An image taken at a distance — 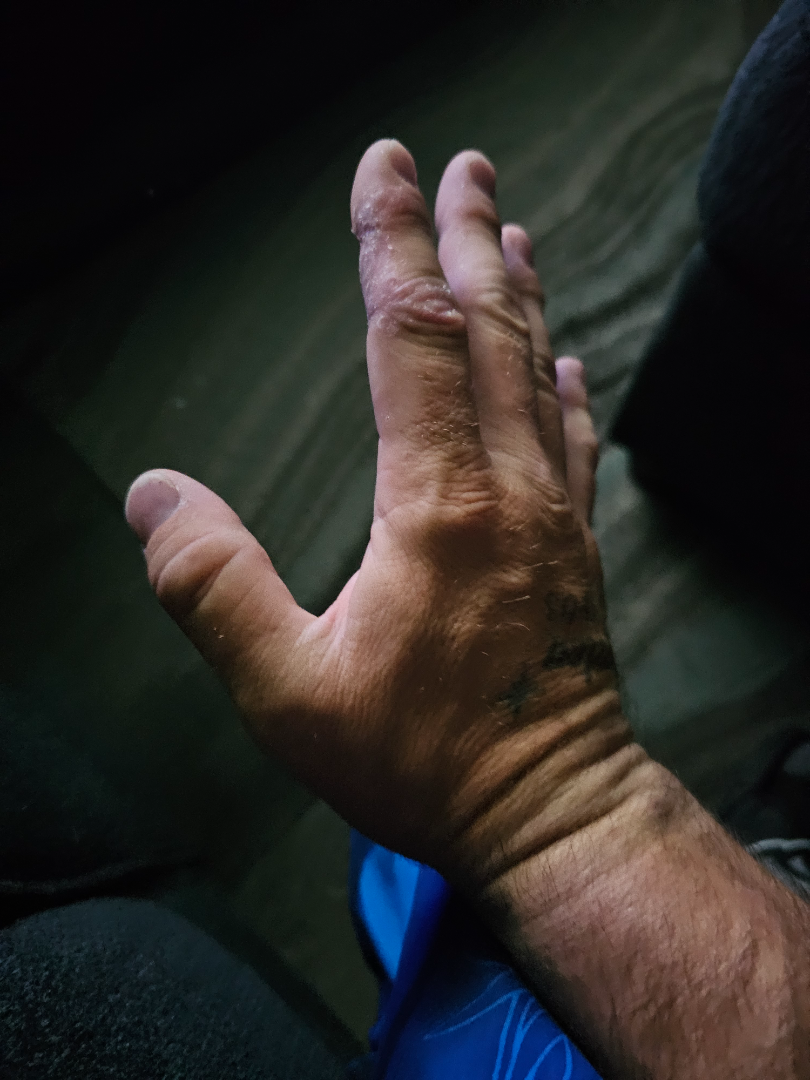Findings:
One reviewing dermatologist: most consistent with Eczema.